This image was taken at an angle: 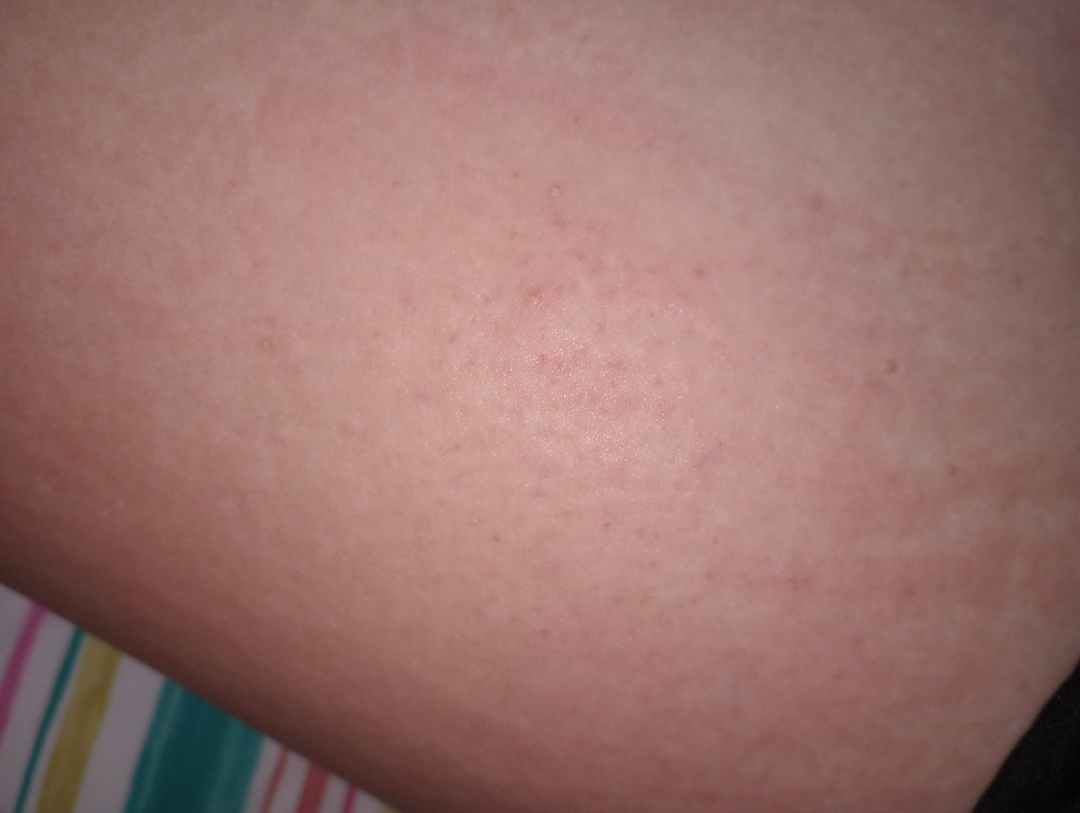The reviewing dermatologist was unable to assign a differential diagnosis from the image.